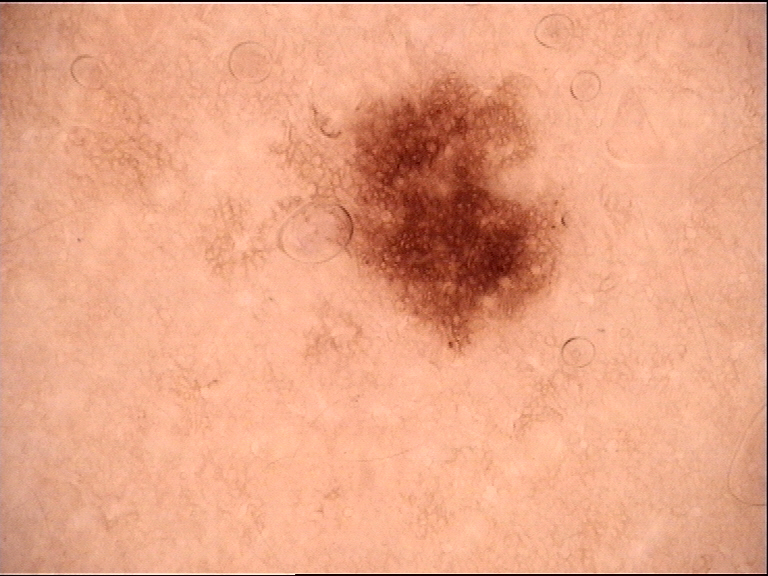- diagnostic label: dysplastic junctional nevus (expert consensus)